A male patient aged 38 to 42 · a dermoscopy image of a single skin lesion:
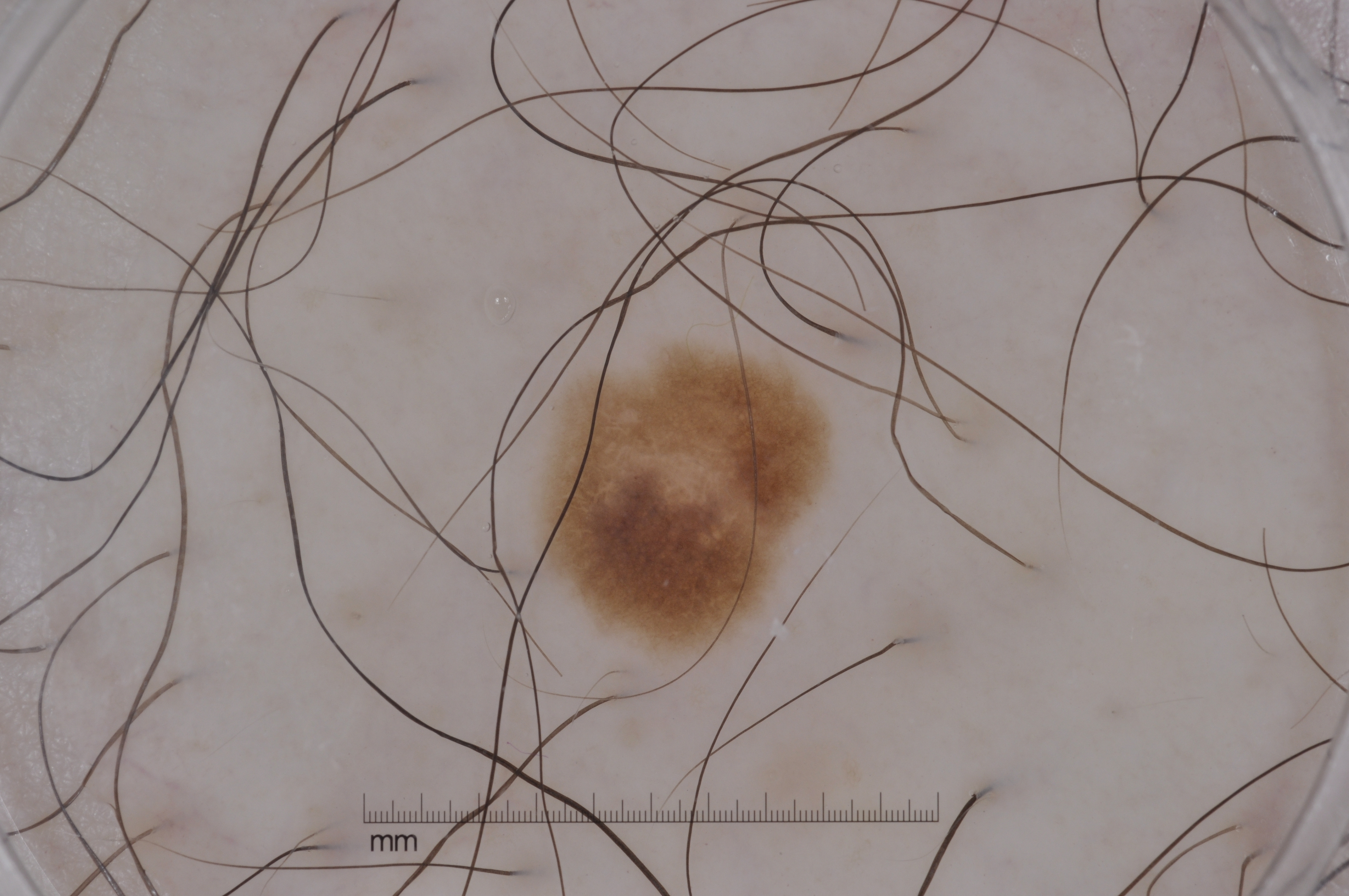{
  "dermoscopic_features": {
    "present": [
      "negative network",
      "pigment network"
    ],
    "absent": [
      "milia-like cysts",
      "streaks"
    ]
  },
  "lesion_location": {
    "bbox_xyxy": [
      526,
      322,
      837,
      683
    ]
  },
  "diagnosis": {
    "name": "melanocytic nevus",
    "malignancy": "benign",
    "lineage": "melanocytic",
    "provenance": "clinical"
  }
}